The contributor is a female aged 40–49 · the lesion involves the leg · the photograph is a close-up of the affected area: 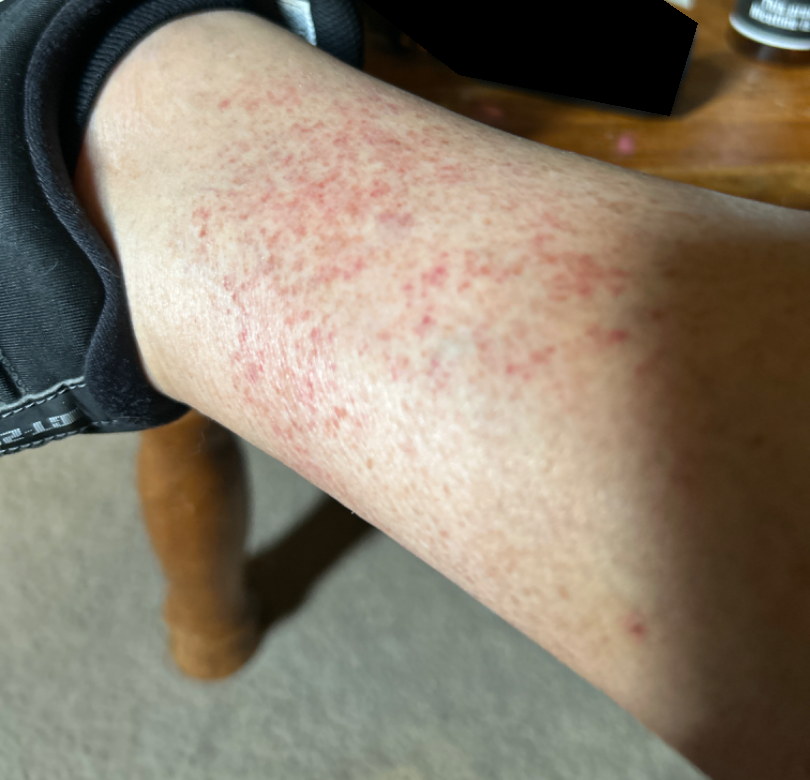No relevant lesion symptoms reported.
The patient also reports fever, fatigue and joint pain.
Self-categorized by the patient as a rash.
Reported duration is less than one week.
Skin tone: FST III.
Texture is reported as flat.
Pigmented purpuric eruption and Leukocytoclastic Vasculitis were each considered, in no particular order.